A dermatoscopic image of a skin lesion.
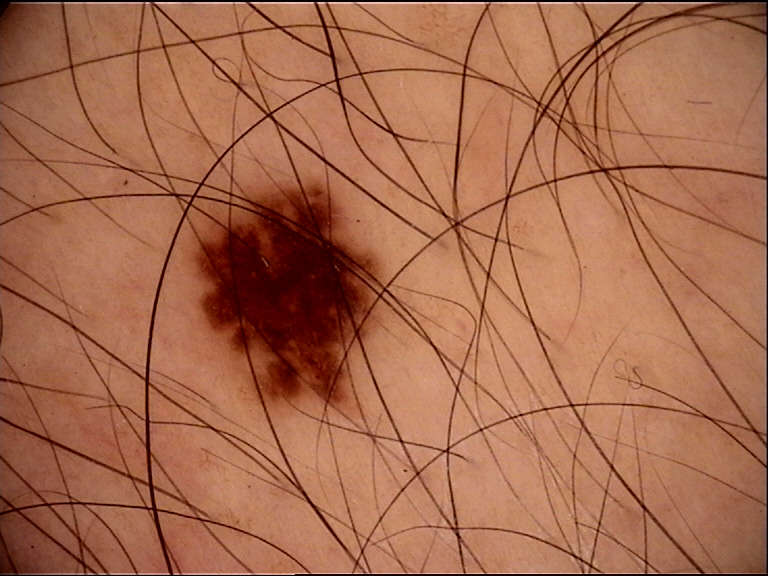Classified as a dysplastic junctional nevus.